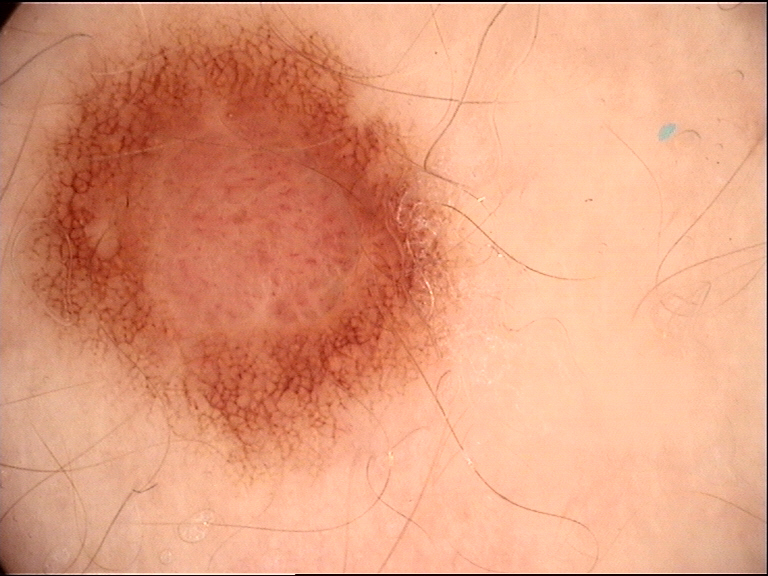A dermoscopic close-up of a skin lesion. This is a banal lesion. Consistent with a compound nevus.